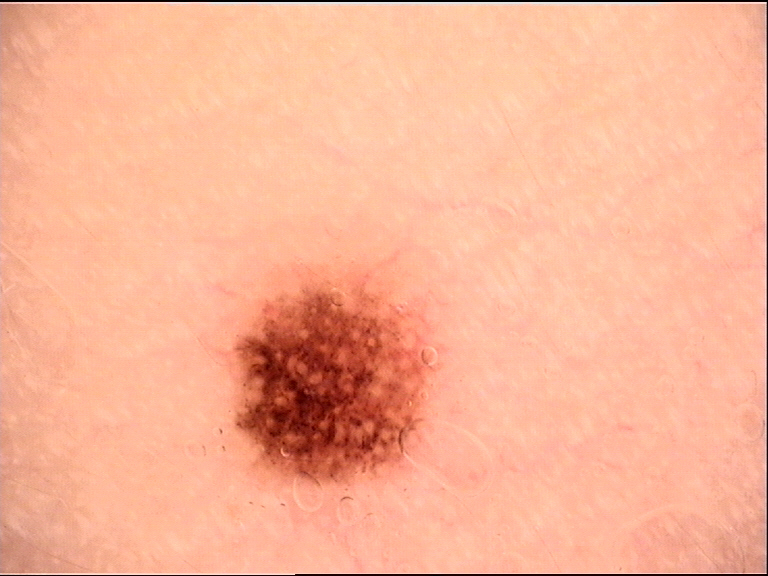image = dermatoscopy, diagnostic label = dysplastic junctional nevus (expert consensus).